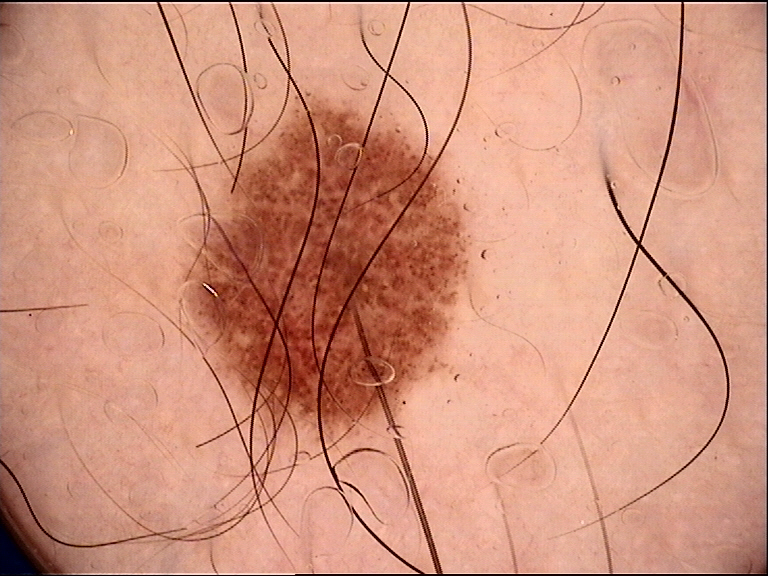Impression: Consistent with a dysplastic junctional nevus.